This image was taken at a distance.
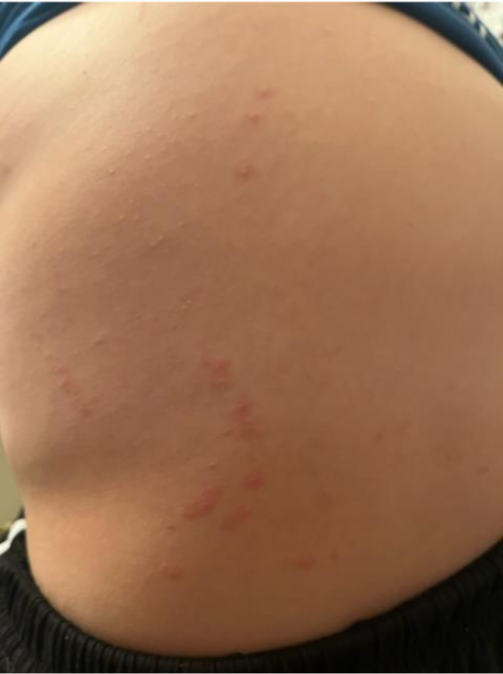Q: What is the dermatologist's impression?
A: in keeping with Eczema